A dermoscopy image of a single skin lesion:
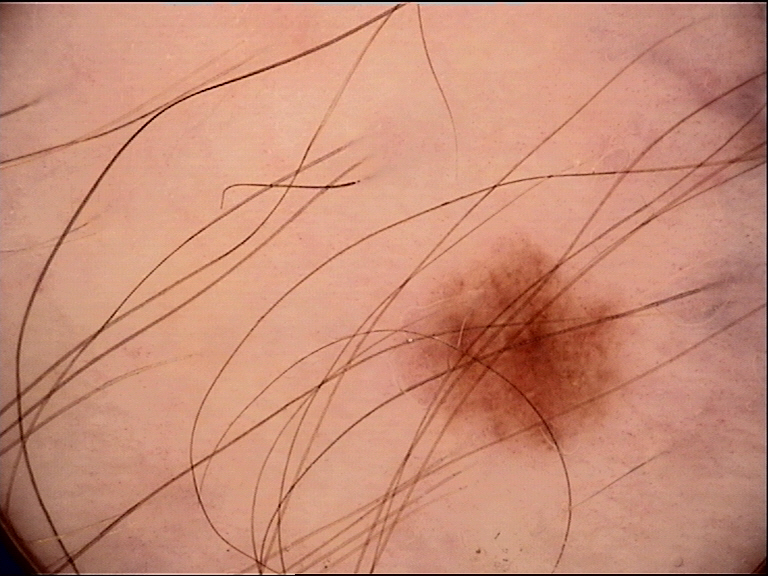• diagnostic label · dysplastic junctional nevus (expert consensus)